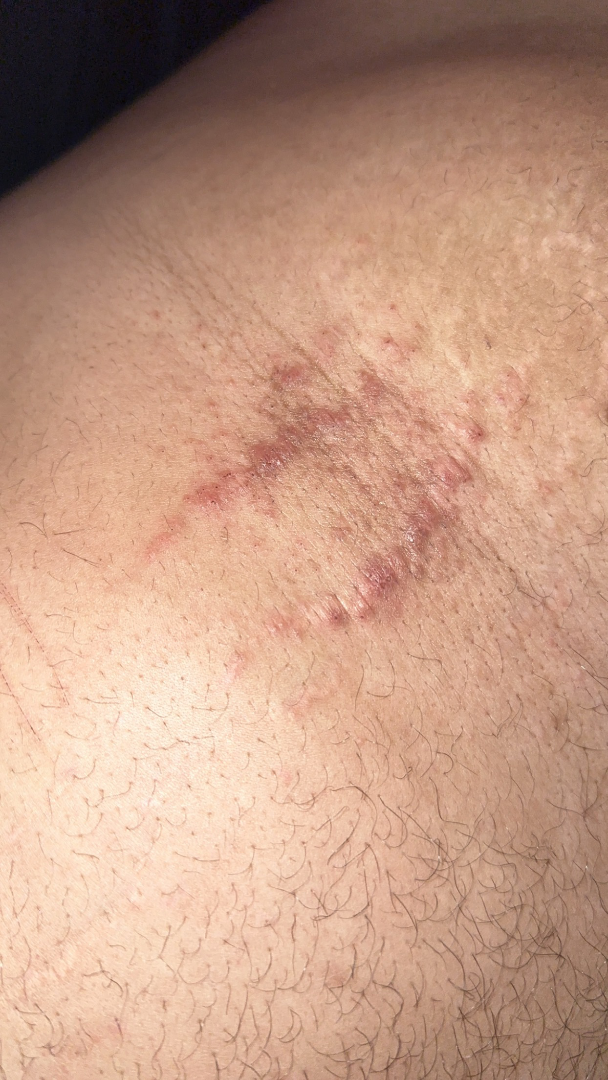Notes:
• assessment — not assessable
• onset — less than one week
• reported symptoms — bothersome appearance, pain and itching
• surface texture — rough or flaky and raised or bumpy
• framing — close-up
• patient's own categorization — a rash